A dermoscopic close-up of a skin lesion.
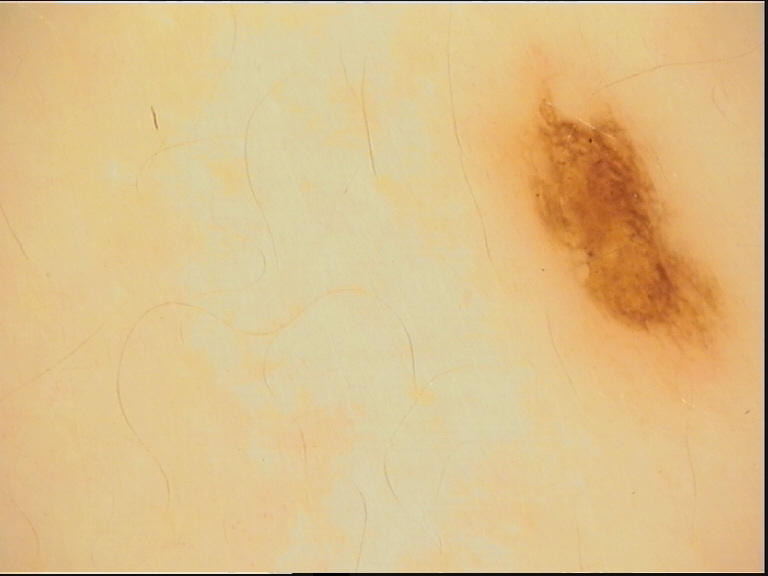Impression:
The diagnostic label was a dysplastic compound nevus.